A female subject 74 years old; recorded as FST II; a clinical photograph of a skin lesion: 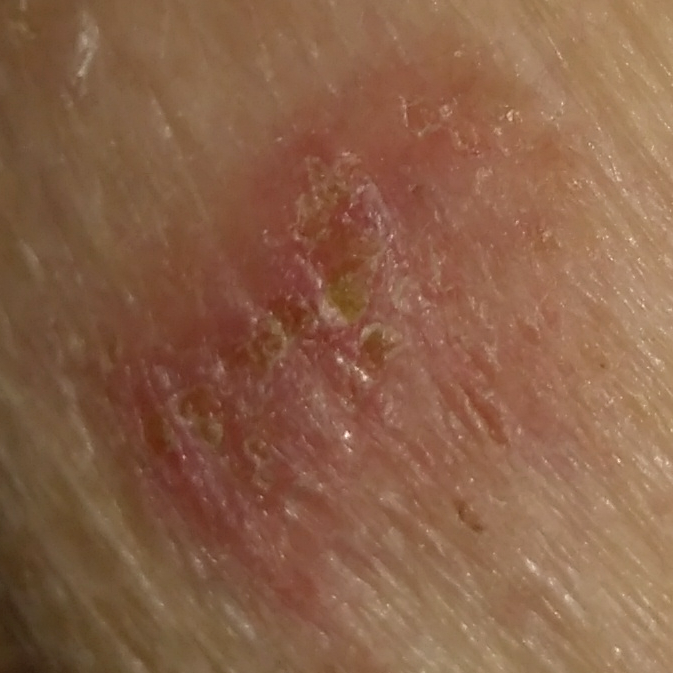anatomic site: an arm | diameter: 14 × 9 mm | patient-reported symptoms: itching / no pain | pathology: basal cell carcinoma (biopsy-proven).